This is a close-up image; located on the head or neck:
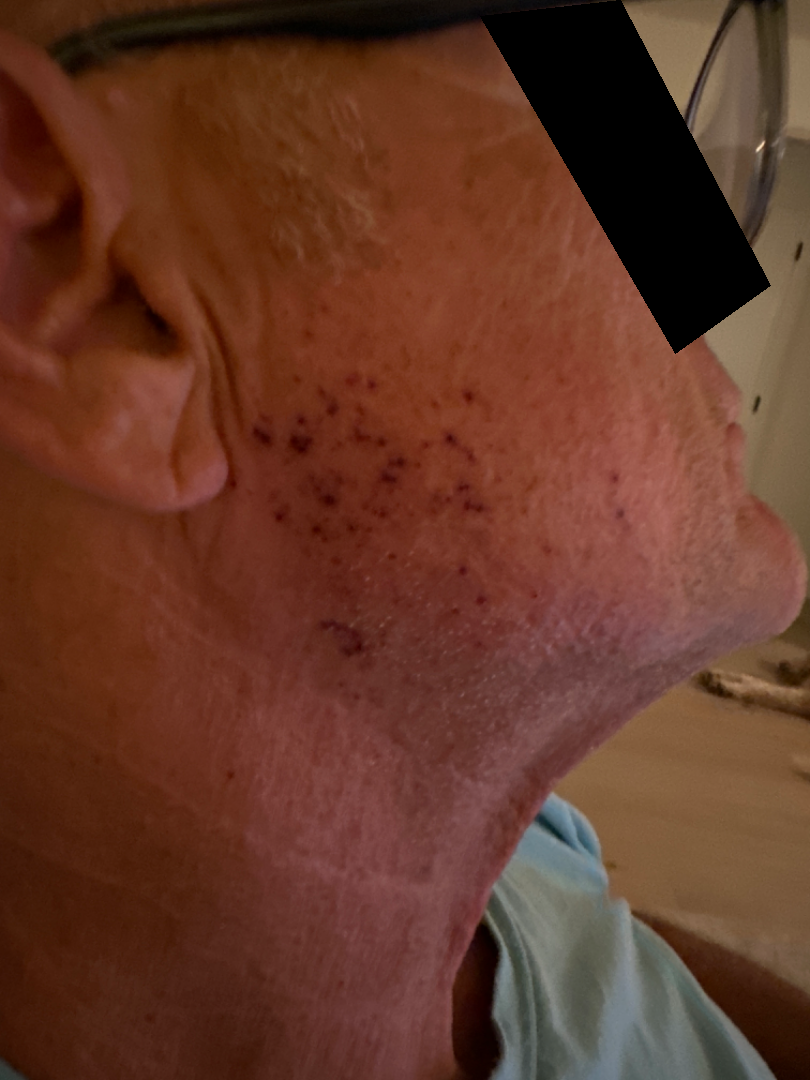Q: Could the case be diagnosed?
A: indeterminate